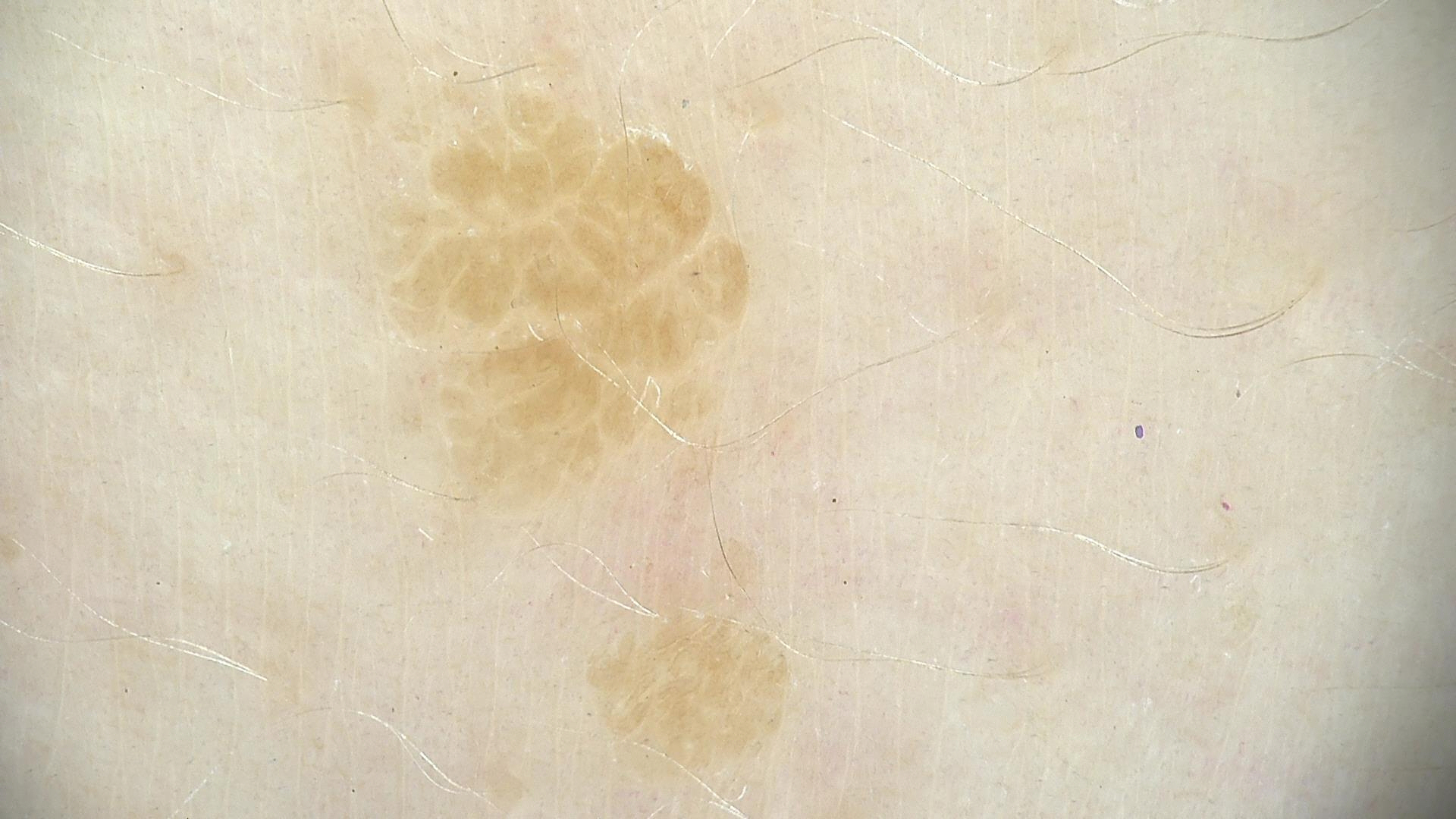Q: What kind of image is this?
A: dermatoscopy
Q: What is the lesion category?
A: keratinocytic
Q: What was the diagnostic impression?
A: seborrheic keratosis (expert consensus)